A dermoscopy image of a single skin lesion: 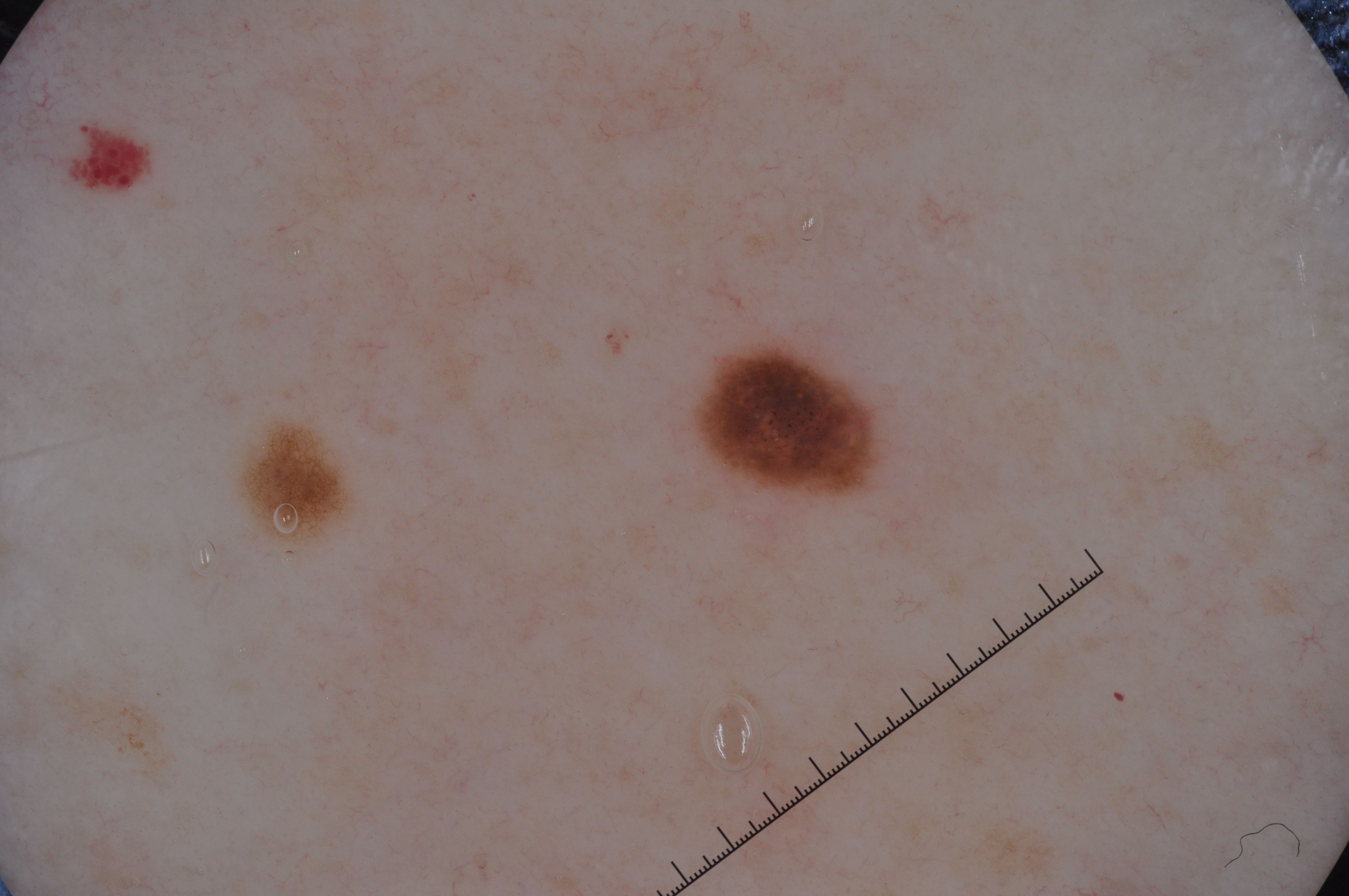The lesion occupies the region <box>695, 343, 875, 497</box>. Clinically diagnosed as a melanocytic nevus.